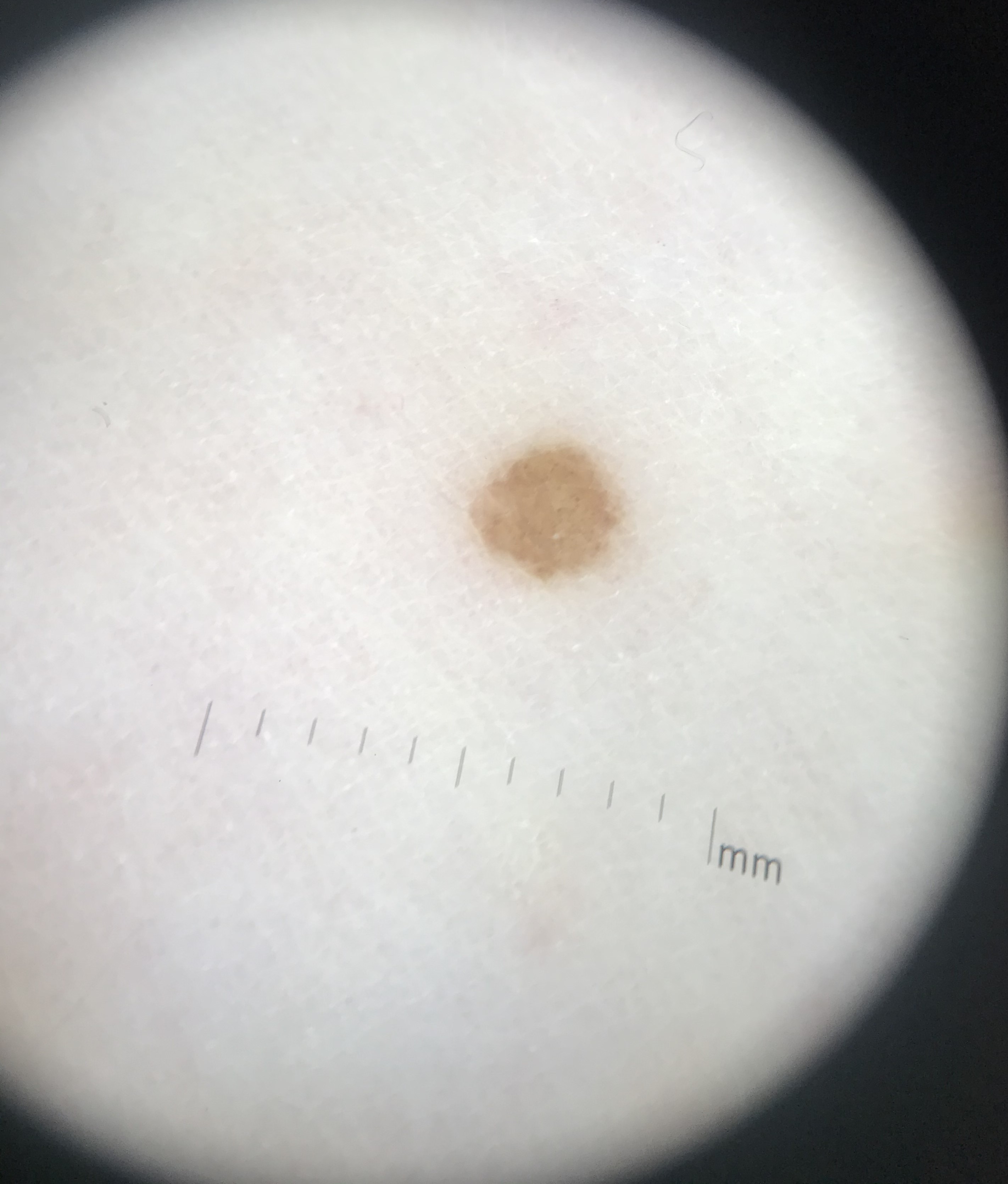Findings: This is a keratinocytic lesion. Conclusion: The diagnosis was a seborrheic keratosis.